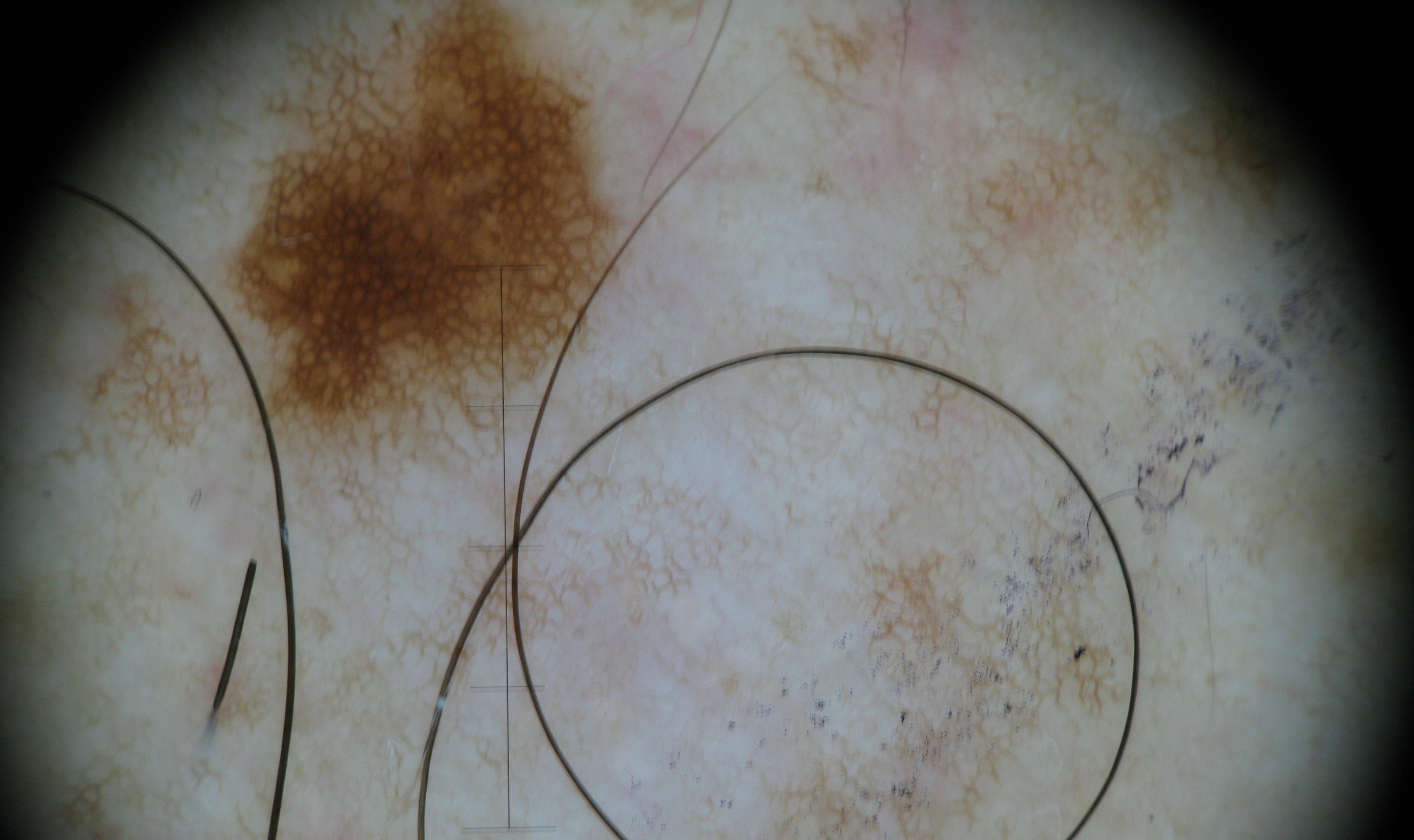modality = dermatoscopy | diagnosis = junctional nevus (expert consensus).